Texture is reported as raised or bumpy. Fitzpatrick II; lay reviewers estimated Monk skin tone scale 1 or 2 (two reviewer pools). Reported duration is about one day. Symptoms reported: burning and itching. The lesion involves the arm, leg and head or neck. An image taken at an angle — 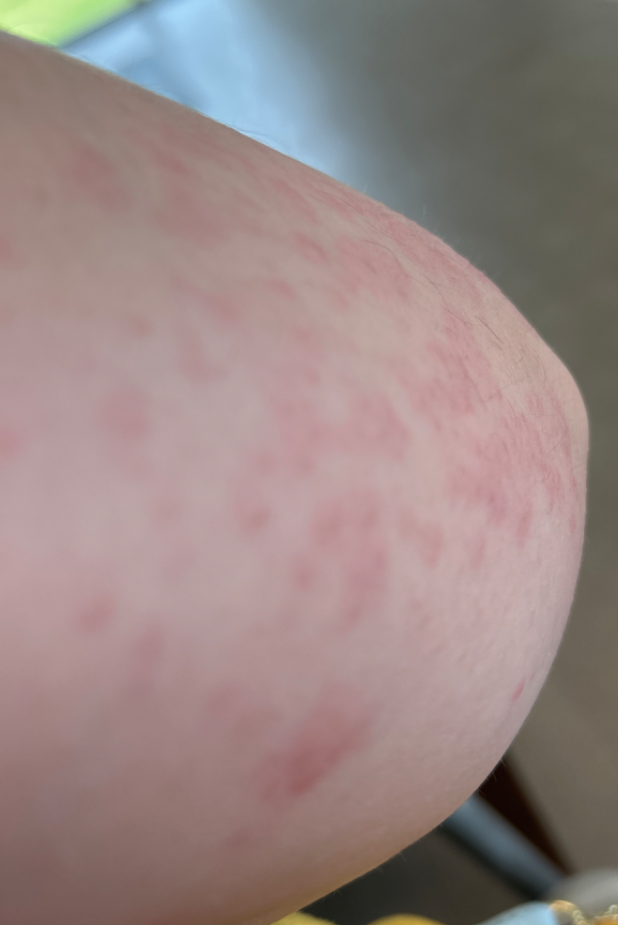The reviewer was unable to grade this case for skin condition.